The photograph was taken at a distance: 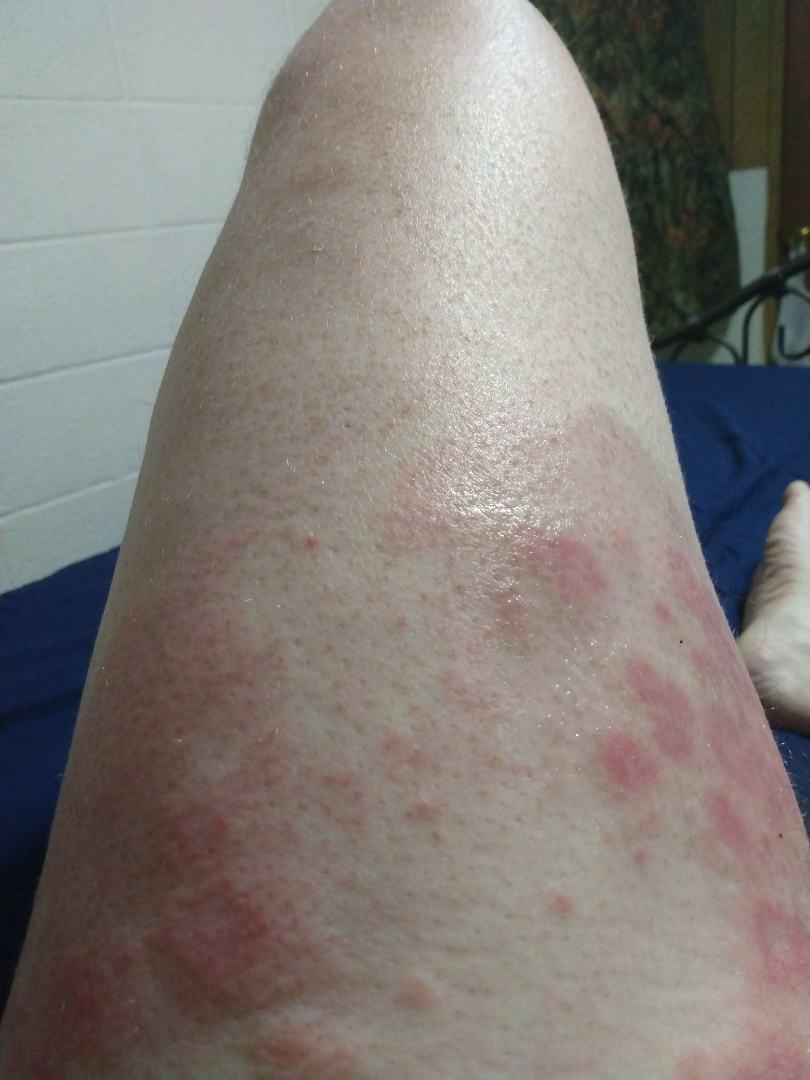differential diagnosis = the leading consideration is Urticaria; also raised was Erythema multiforme; an alternative is Allergic Contact Dermatitis